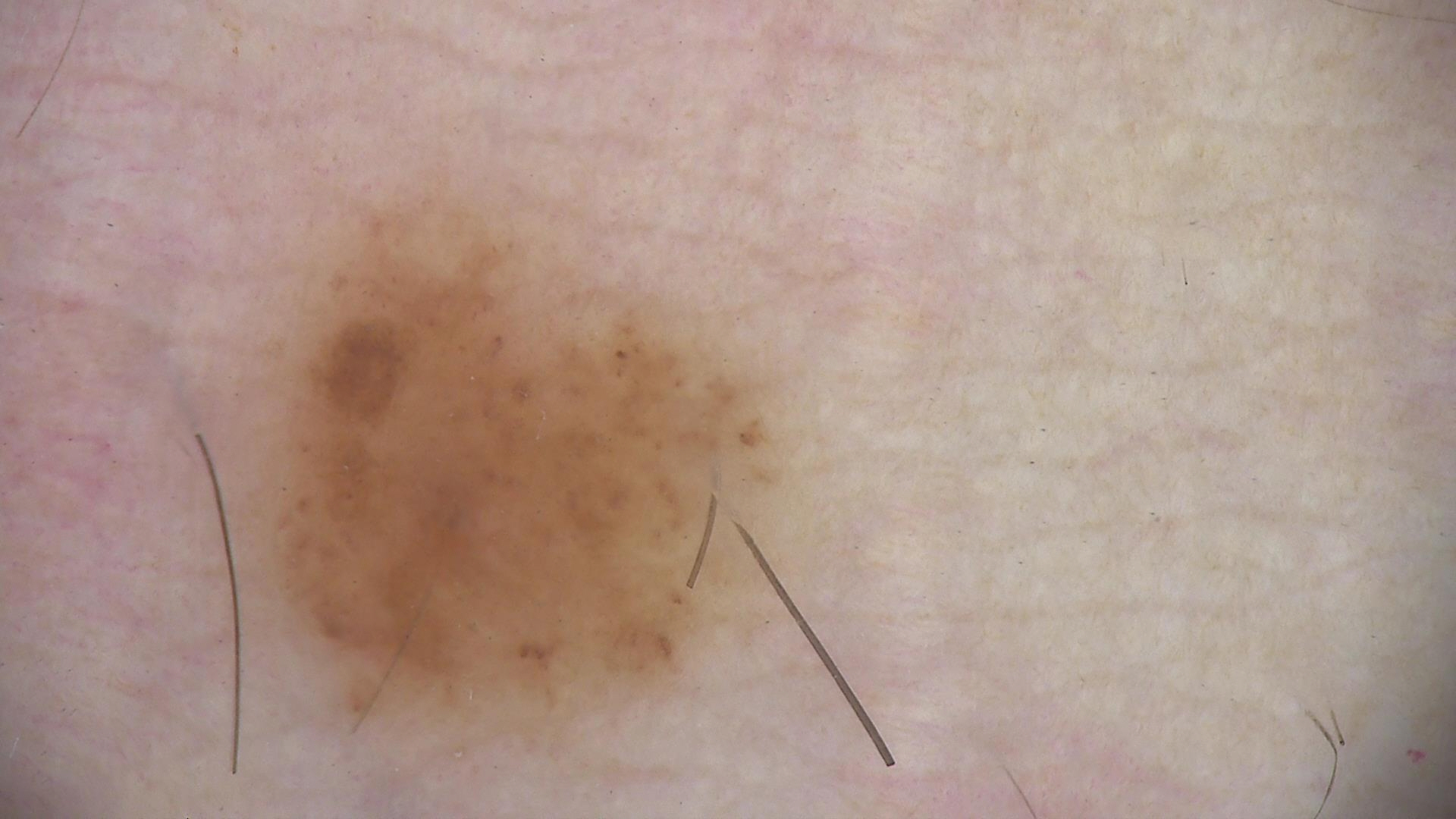A dermoscopic close-up of a skin lesion.
Classified as a dysplastic junctional nevus.